Male contributor, age 30–39; a close-up photograph; located on the arm: 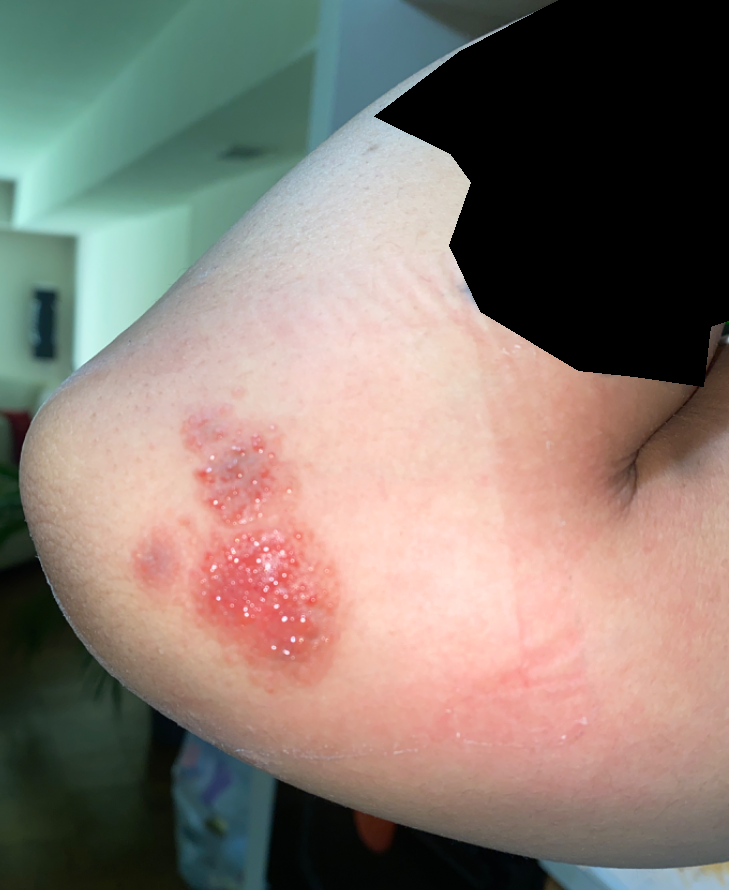Q: What is the differential diagnosis?
A: a single dermatologist reviewed the case: favoring Herpes Zoster; with consideration of Allergic Contact Dermatitis; less likely is Herpes Simplex